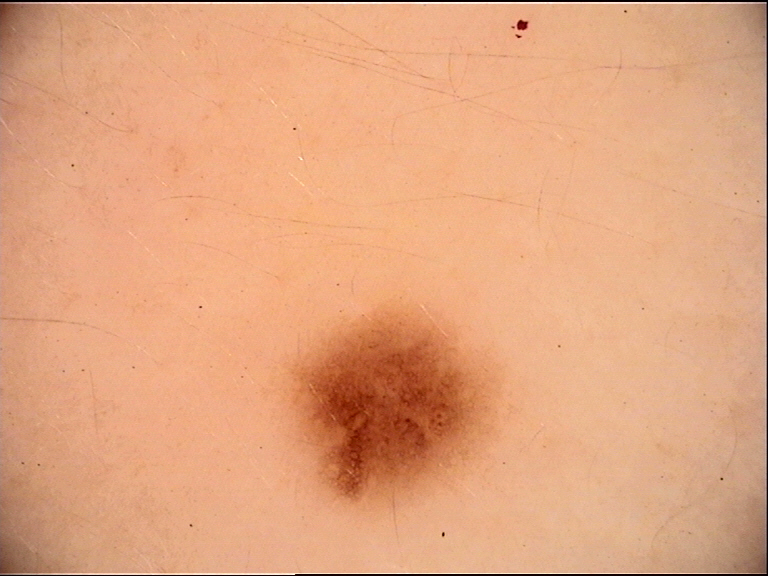Diagnosed as a dysplastic junctional nevus.